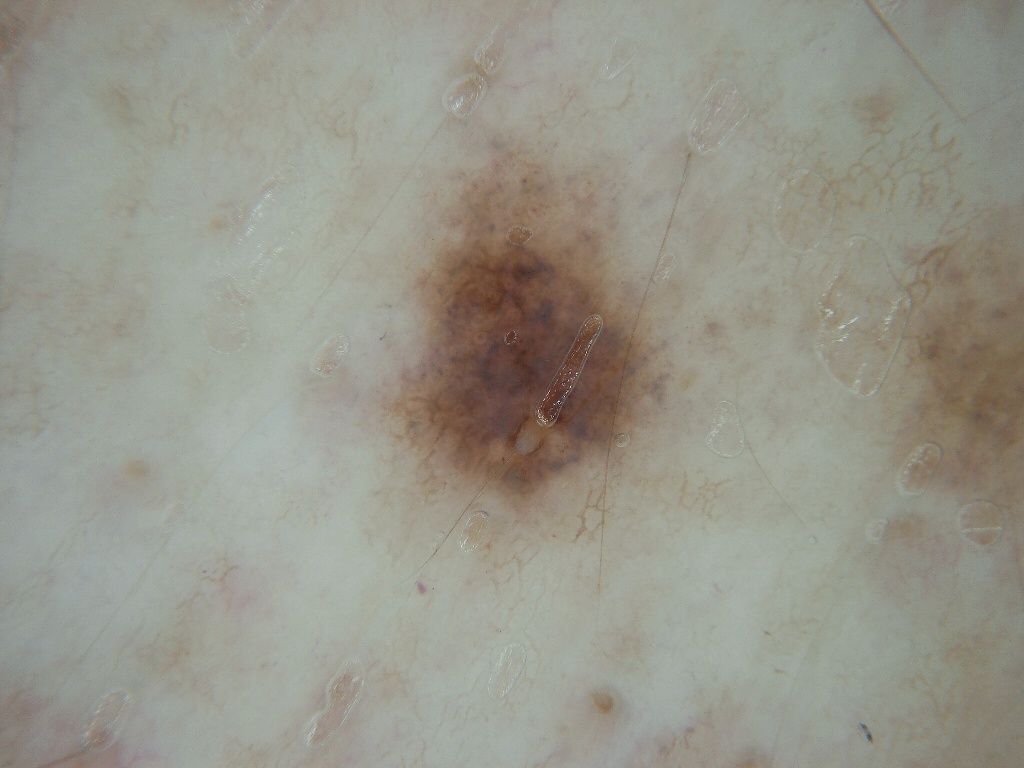subject — male, in their mid- to late 60s | imaging — dermatoscopic image of a skin lesion | lesion bbox — (358, 112, 684, 577) | dermoscopic pattern — pigment network; absent: globules, negative network, milia-like cysts, and streaks | assessment — a melanocytic nevus, a benign lesion.